Present for less than one week, the photograph was taken at an angle, the patient described the issue as a rash, FST II:
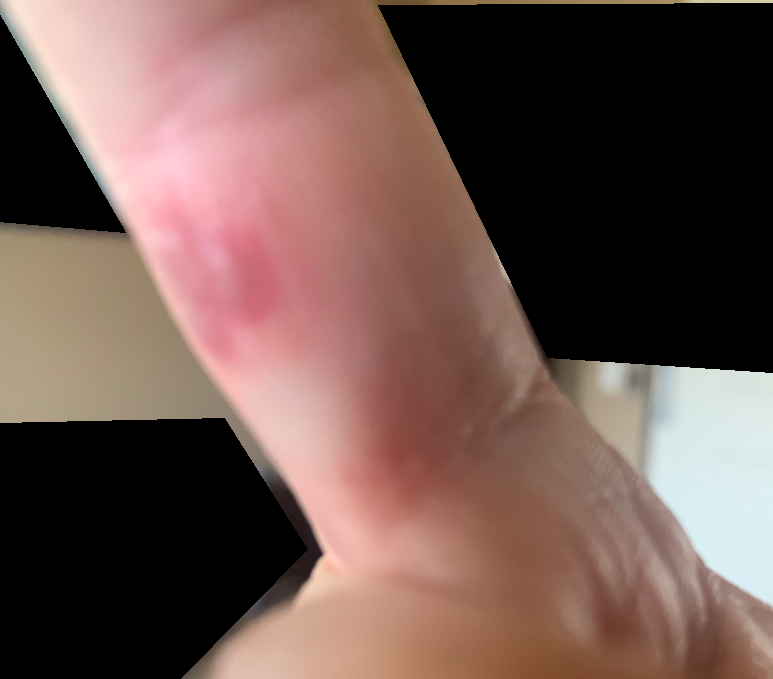On remote dermatologist review, favoring Herpes Simplex; with consideration of Insect Bite; an alternative is Eczema.